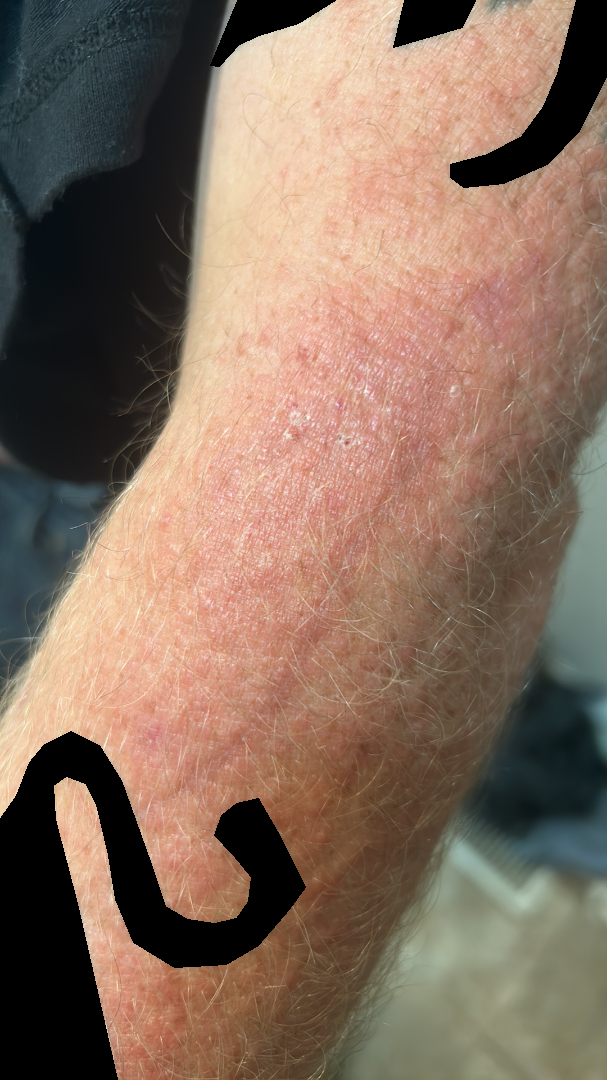Impression: Psoriasis and Eczema were considered with similar weight.